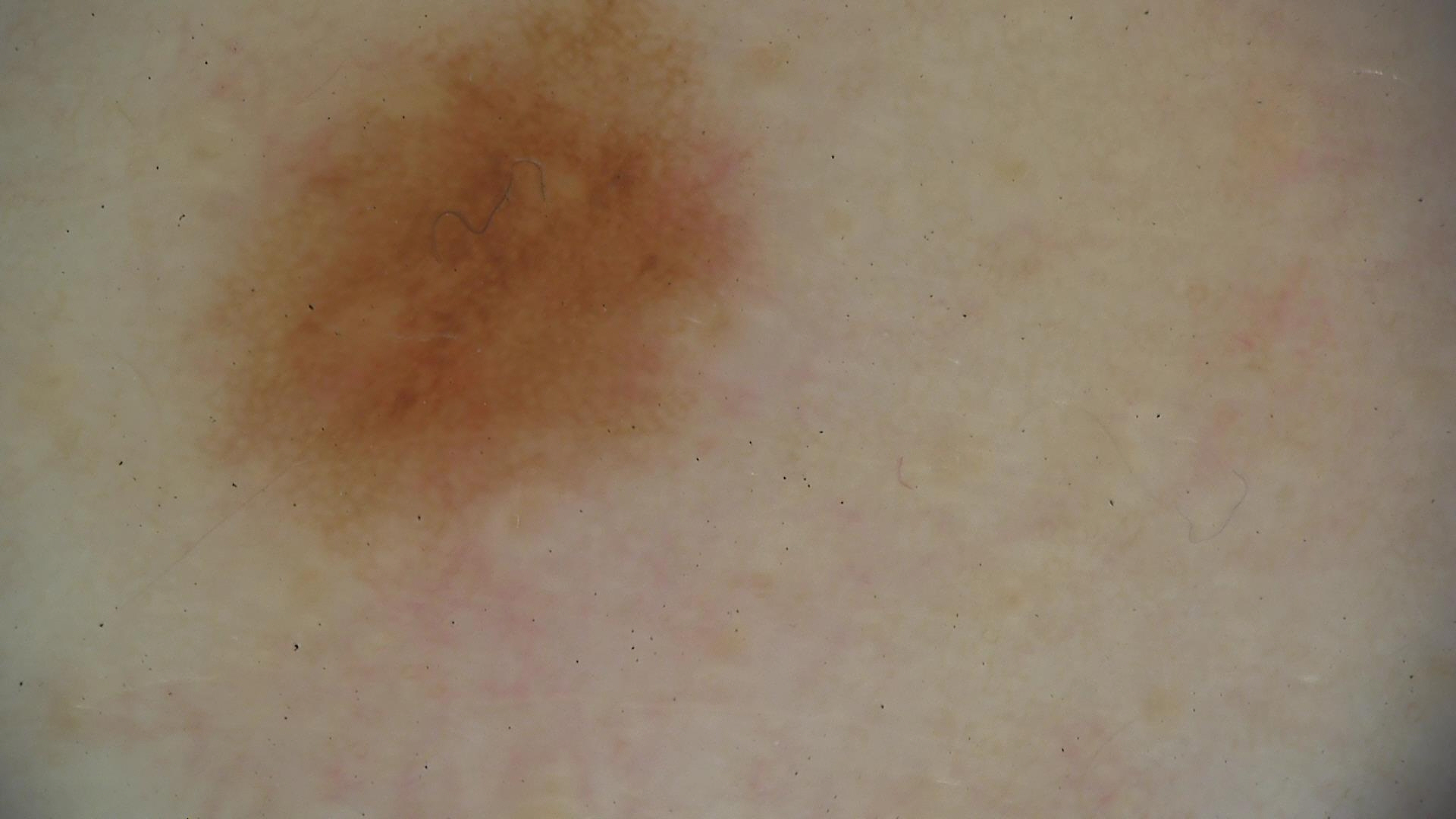Case: A dermoscopic close-up of a skin lesion. Impression: Classified as a benign lesion — a dysplastic junctional nevus.